A dermoscopic close-up of a skin lesion.
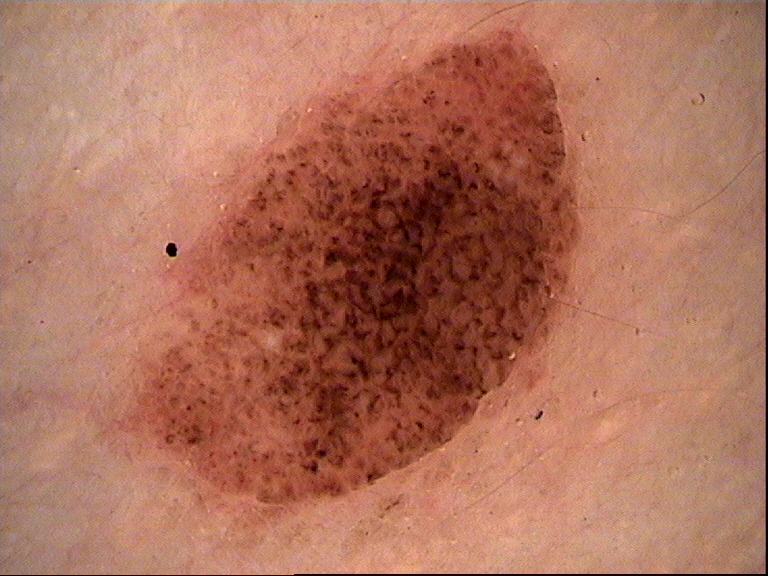Case: The morphology is that of a banal lesion. Conclusion: Classified as a compound nevus.